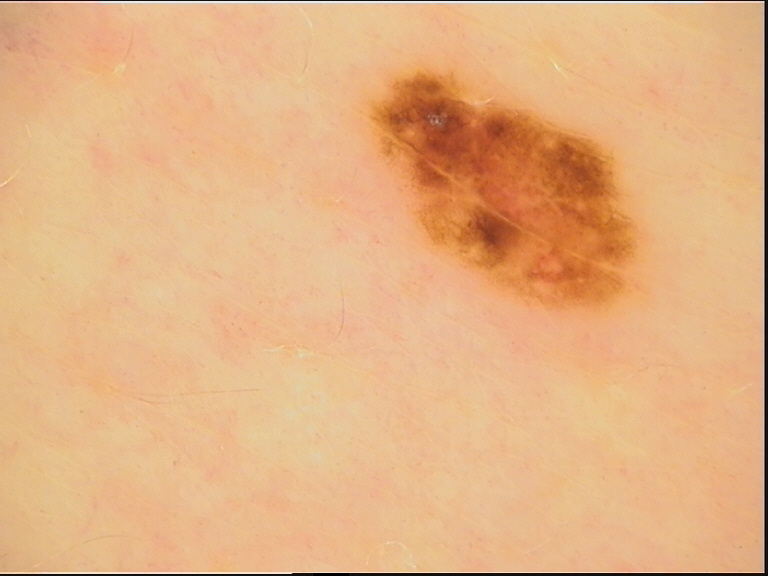diagnosis = dysplastic compound nevus (expert consensus).